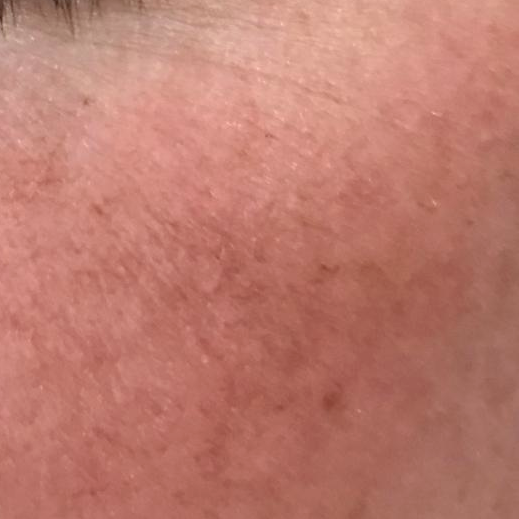Case summary:
A clinical photo of a skin lesion taken with a smartphone. A subject 38 years old. The lesion was found on the face. Asymptomatic by report.
Conclusion:
Expert review favored an actinic keratosis.